A dermoscopy image of a single skin lesion: 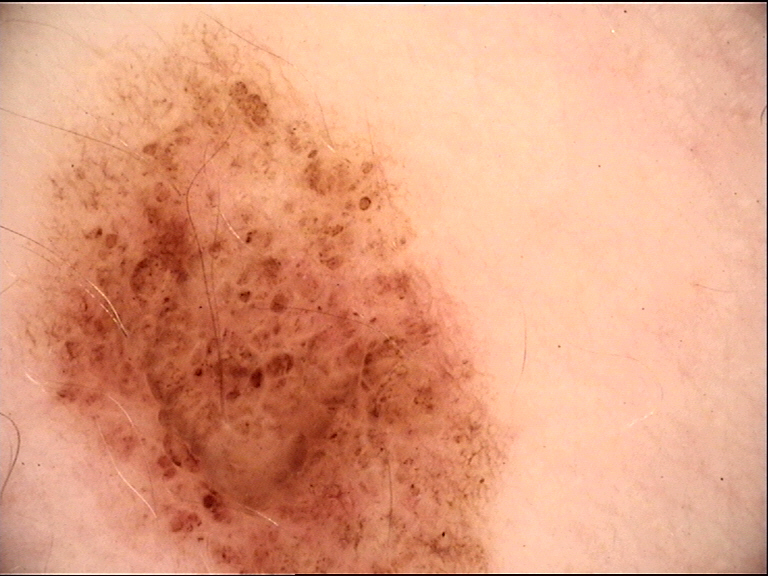classification: banal; diagnostic label: compound nevus (expert consensus).